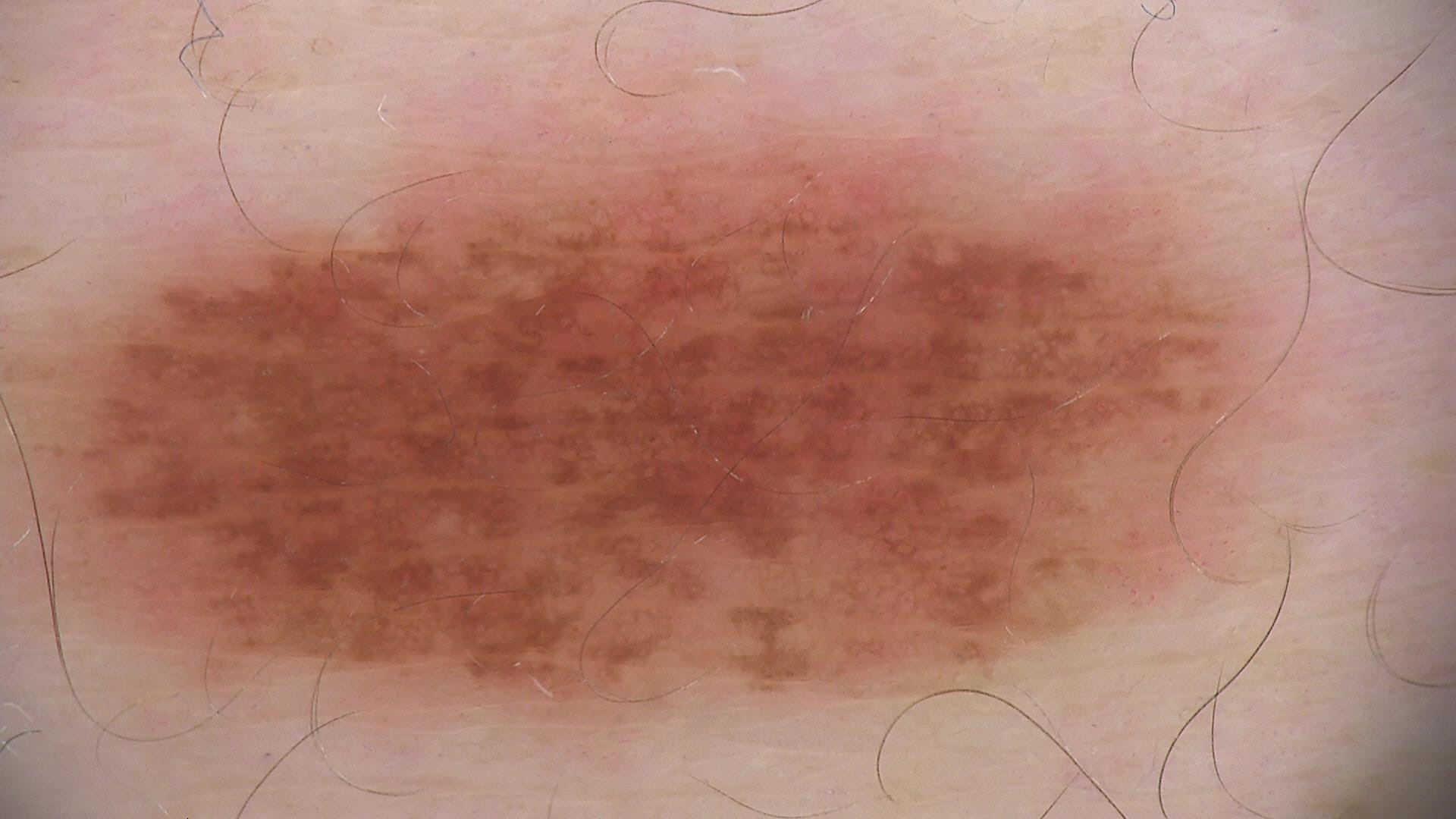  diagnosis:
    name: dysplastic junctional nevus
    code: jd
    malignancy: benign
    super_class: melanocytic
    confirmation: expert consensus